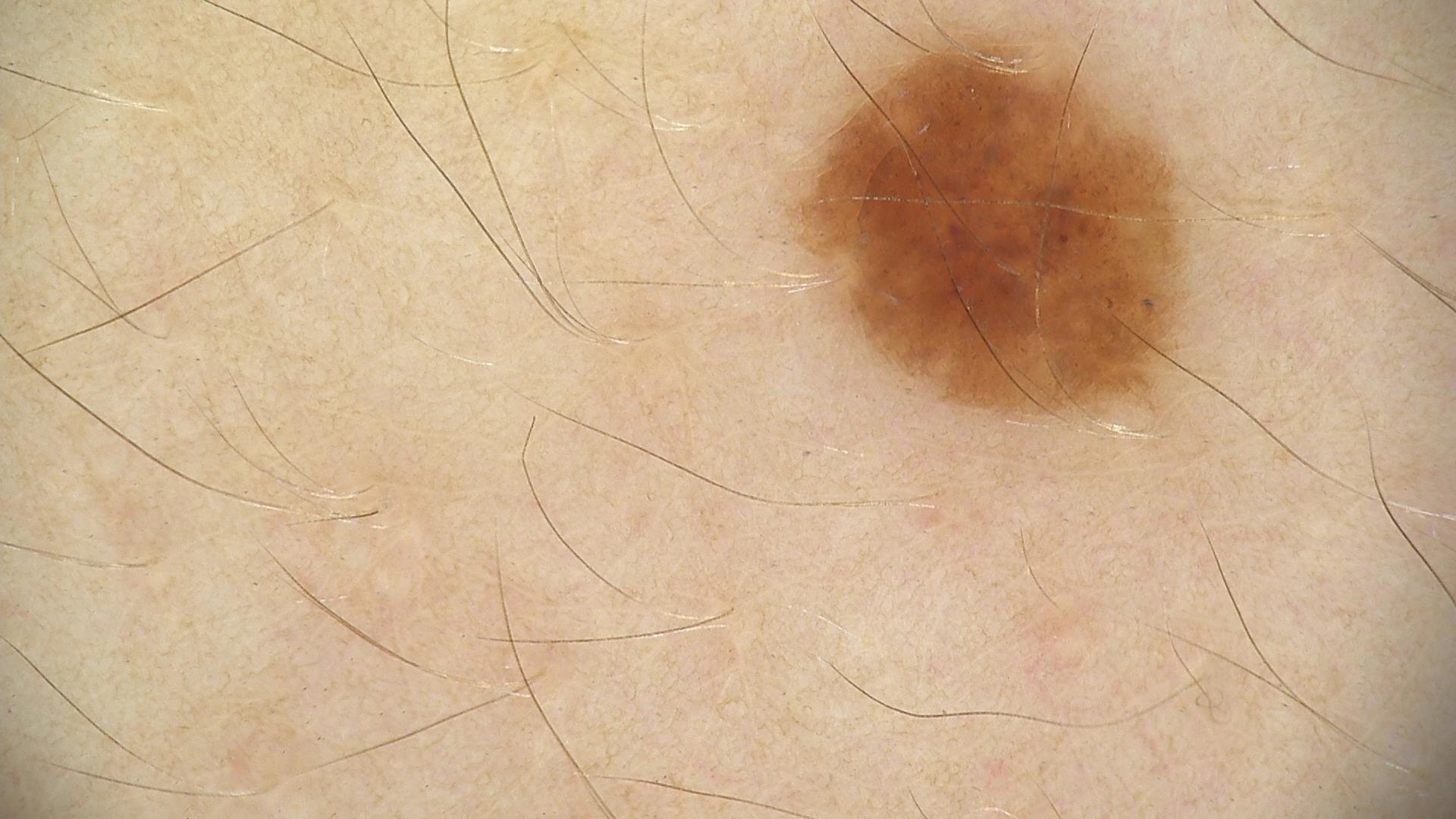imaging = dermoscopy; label = dysplastic junctional nevus (expert consensus).